The photo was captured at a distance. The lesion involves the front of the torso: 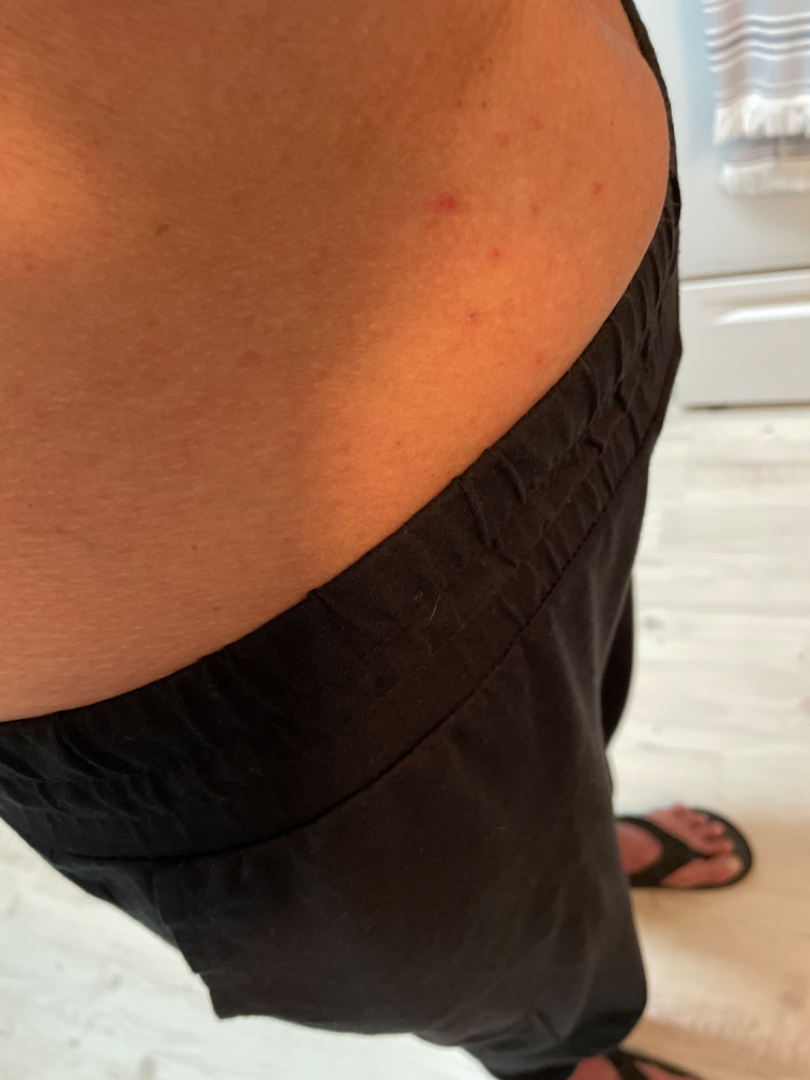No differential diagnosis could be assigned on photographic review.